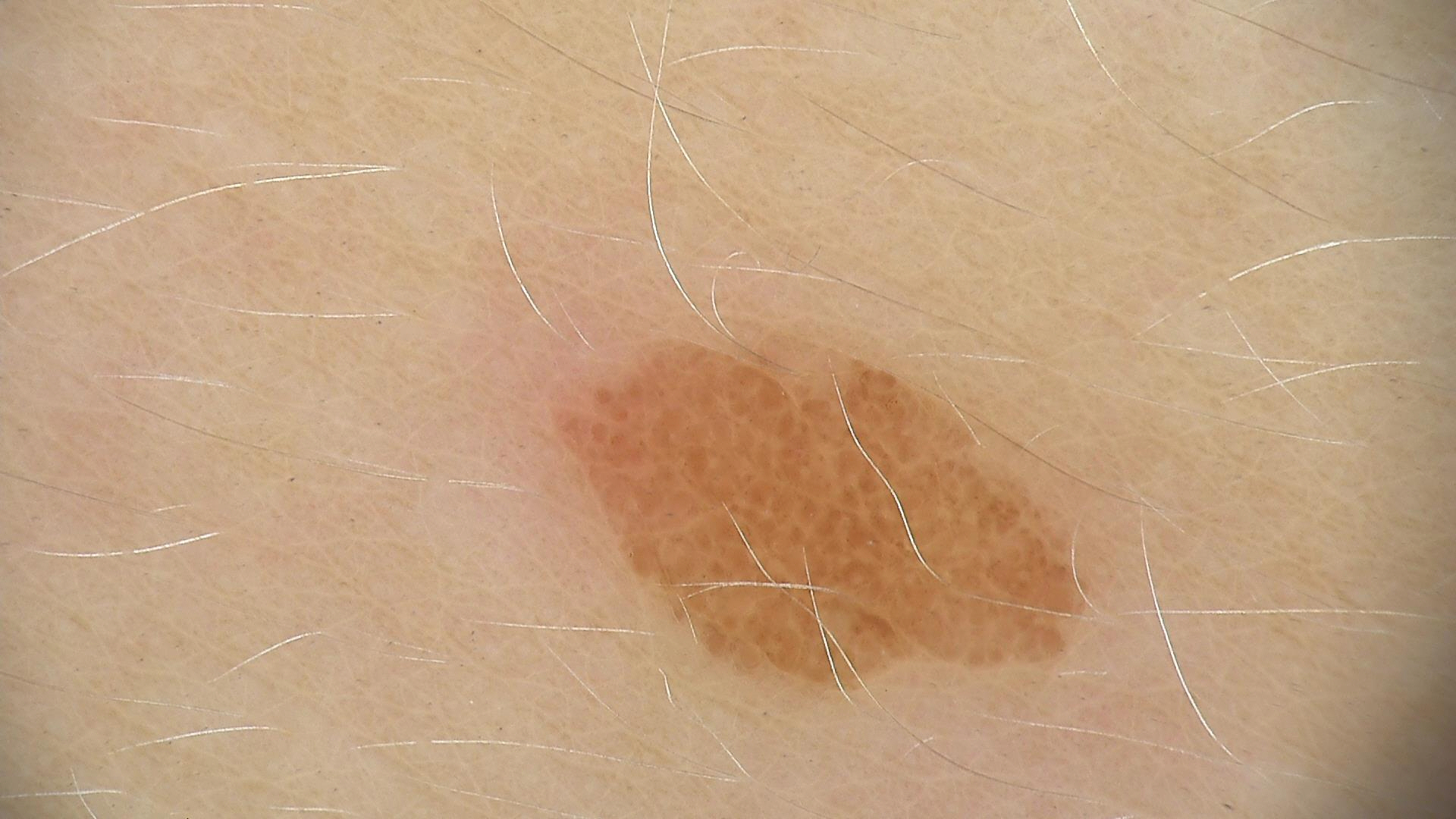diagnosis: dysplastic junctional nevus (expert consensus).